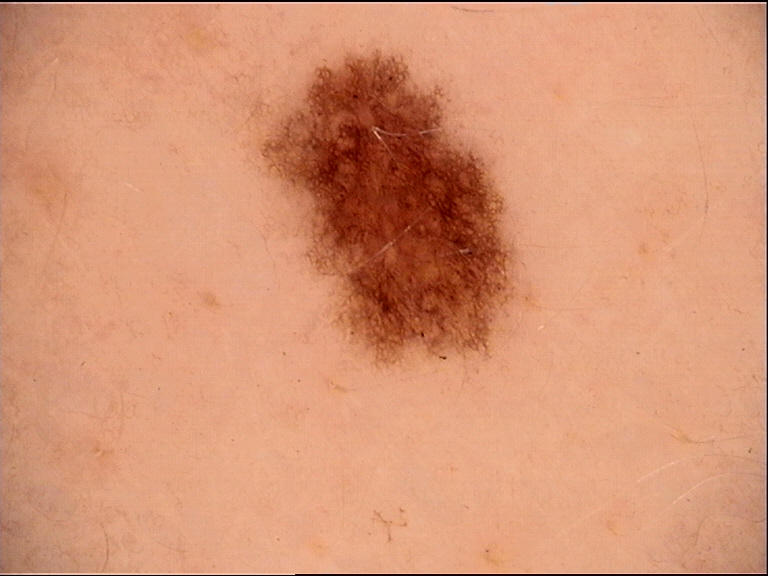{"image": "dermoscopy", "diagnosis": {"name": "dysplastic junctional nevus", "code": "jd", "malignancy": "benign", "super_class": "melanocytic", "confirmation": "expert consensus"}}